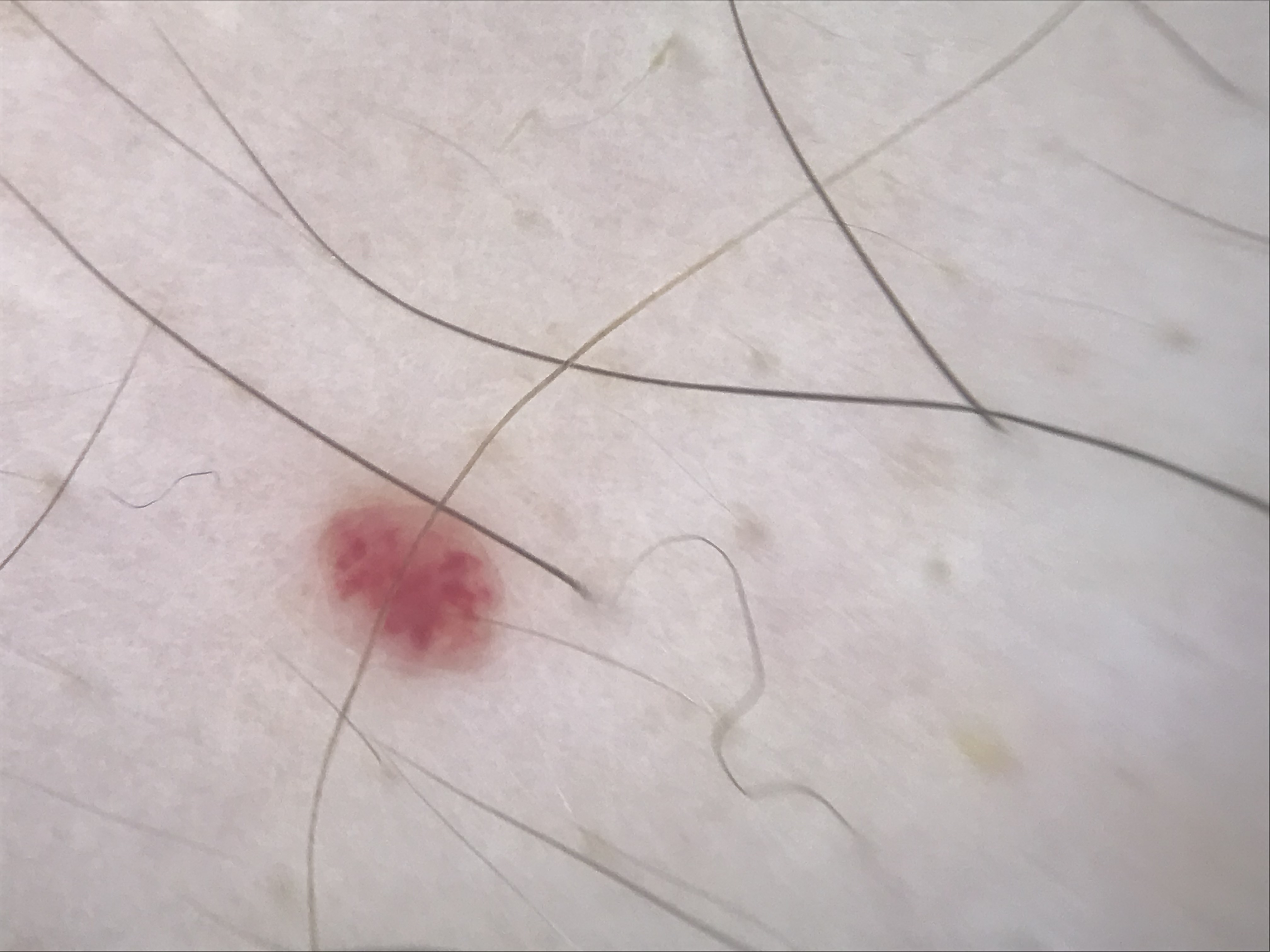Q: What kind of image is this?
A: dermoscopy
Q: What kind of lesion is this?
A: vascular
Q: What is this lesion?
A: hemangioma (expert consensus)